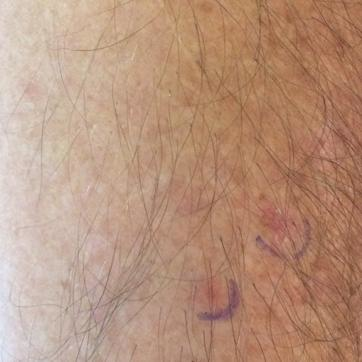Findings:
– subject: in their mid-30s
– region: a forearm
– impression: actinic keratosis (clinical consensus)